A dermatoscopic image of a skin lesion: 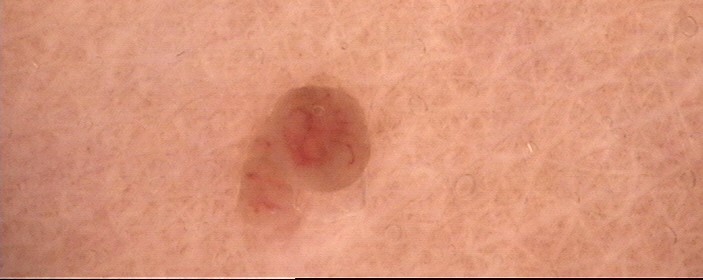The diagnostic label was a banal lesion — a dermal nevus.